A dermoscopic image of a skin lesion.
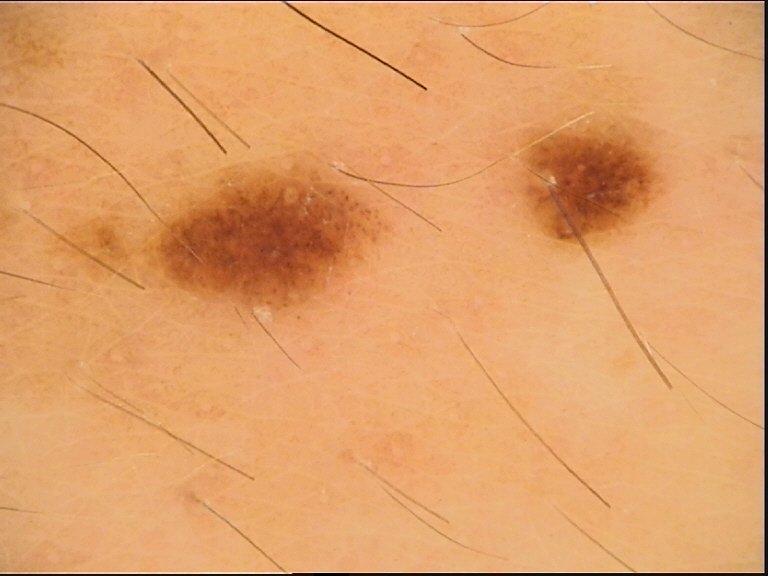Q: What is the diagnosis?
A: dysplastic junctional nevus (expert consensus)